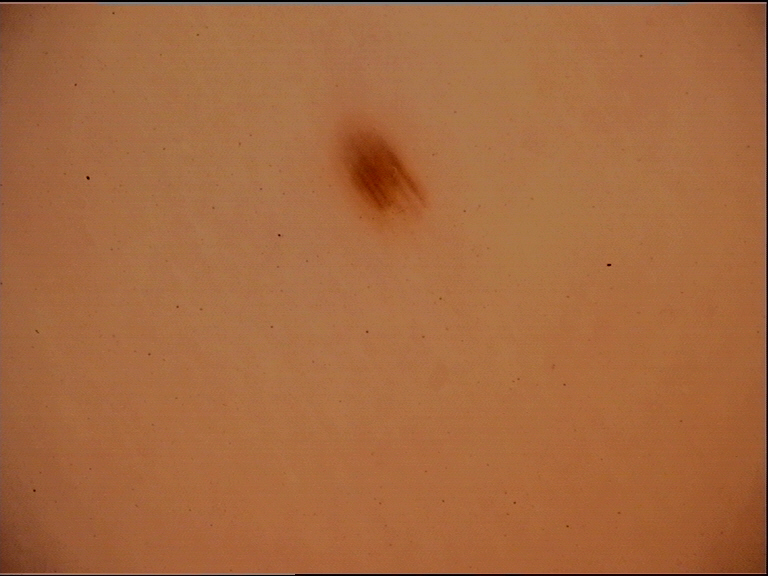– imaging · dermoscopy
– class · acral junctional nevus (expert consensus)